A subject in their 40s. A clinical photograph showing a skin lesion.
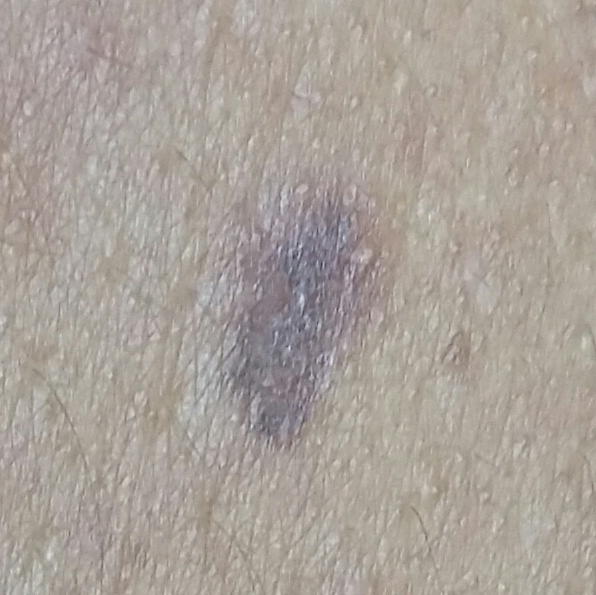Notes:
– body site: the back
– symptoms: itching, growth, change in appearance
– diagnostic label: nevus (clinical consensus)